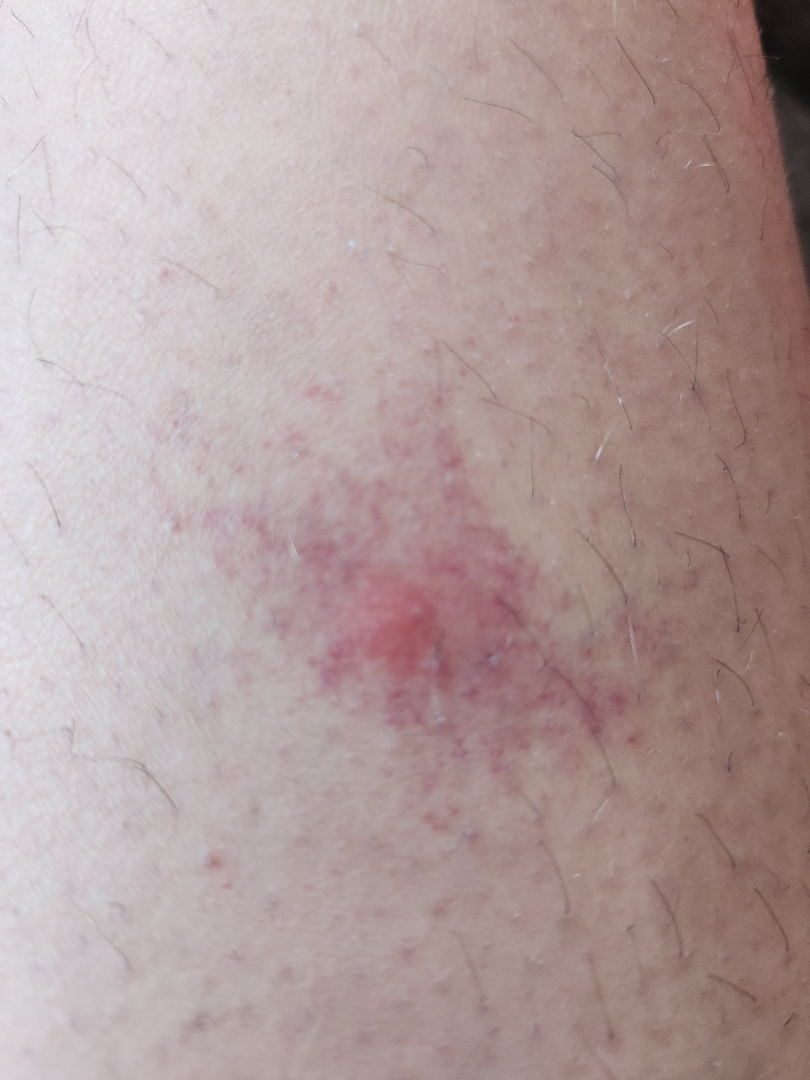impression=reviewed remotely by one dermatologist: the leading consideration is Insect Bite; an alternative is Abscess